A clinical photograph showing a skin lesion · the patient says their skin tans without first burning · a female patient age 78 · collected as part of a research study, without a referral diagnosis · the patient describes having numerous moles.
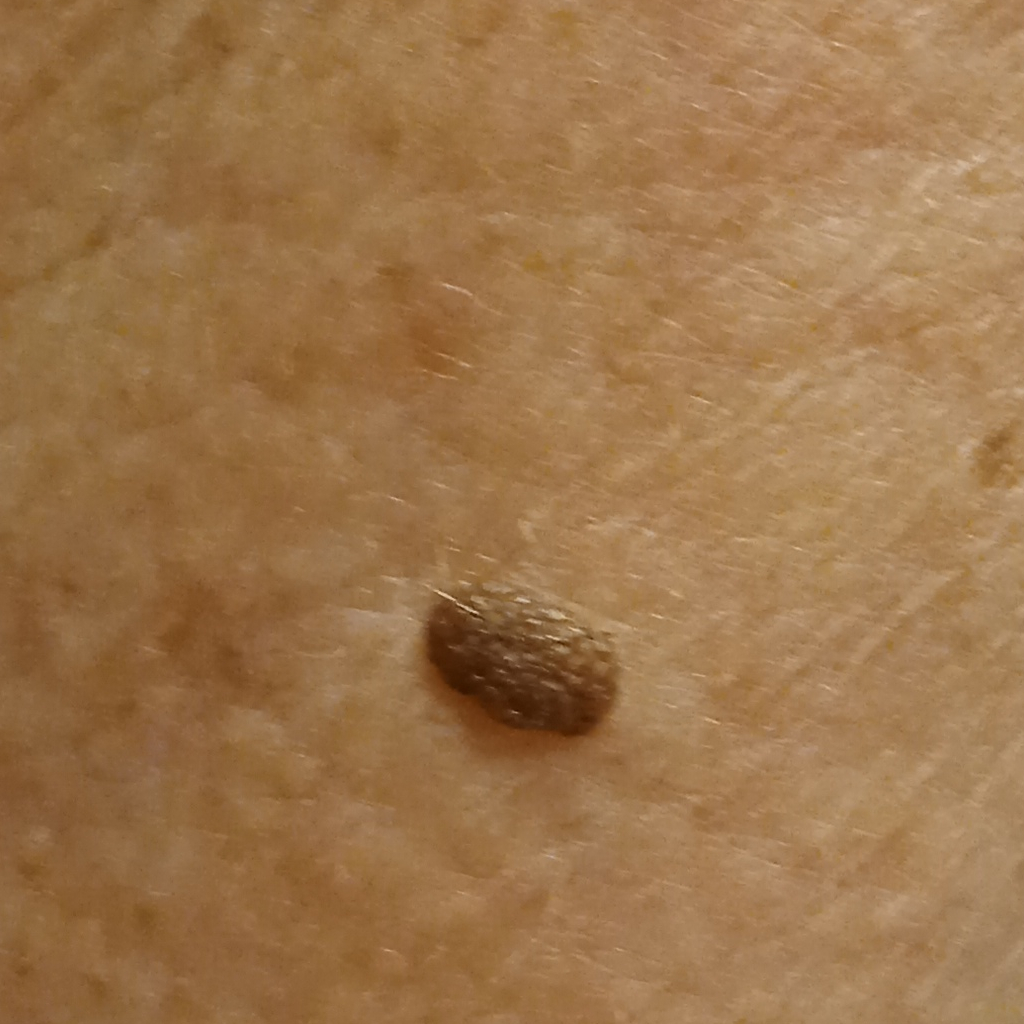The lesion is located on an arm. The lesion is about 5.6 mm across. The consensus diagnosis for this lesion was a seborrheic keratosis.